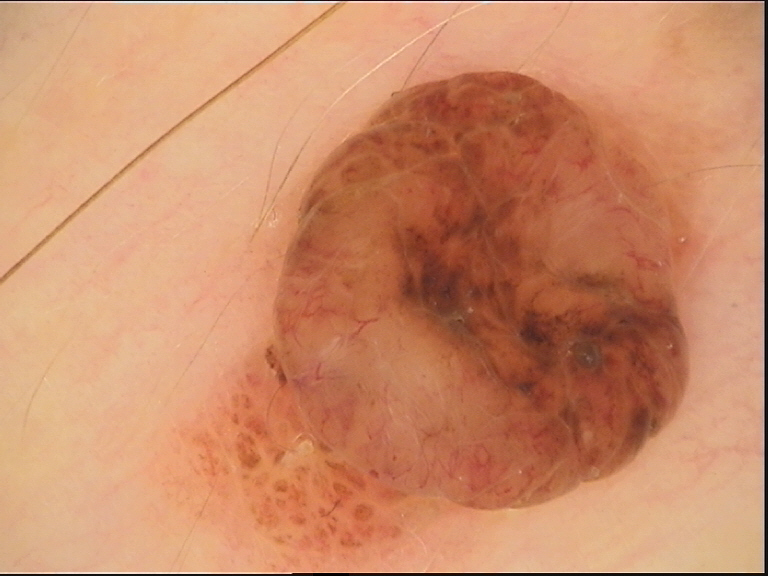A skin lesion imaged with a dermatoscope. The architecture is that of a banal lesion. Diagnosed as a dermal nevus.